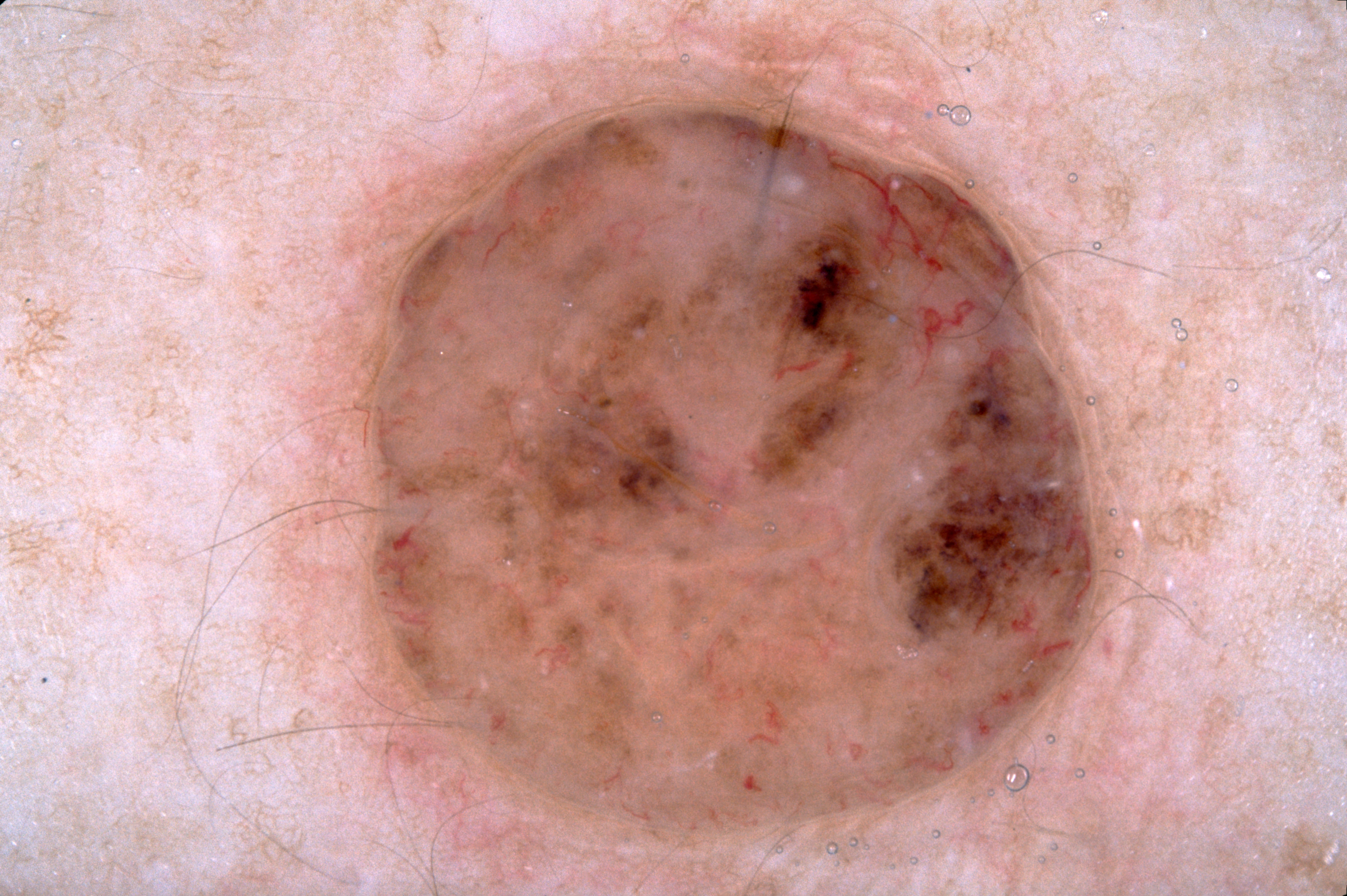Q: What is the imaging modality?
A: dermatoscopic image of a skin lesion
Q: Patient demographics?
A: female, aged 48 to 52
Q: What is notable about the lesion's margin?
A: clipped at the frame edge
Q: What is the lesion's bounding box?
A: bbox=[269, 18, 1145, 895]
Q: What dermoscopic features are not present?
A: milia-like cysts, negative network, pigment network, and streaks
Q: How much of the field does the lesion occupy?
A: ~42% of the field
Q: What is the diagnosis?
A: a melanocytic nevus